A close-up photograph. Skin tone: FST IV: 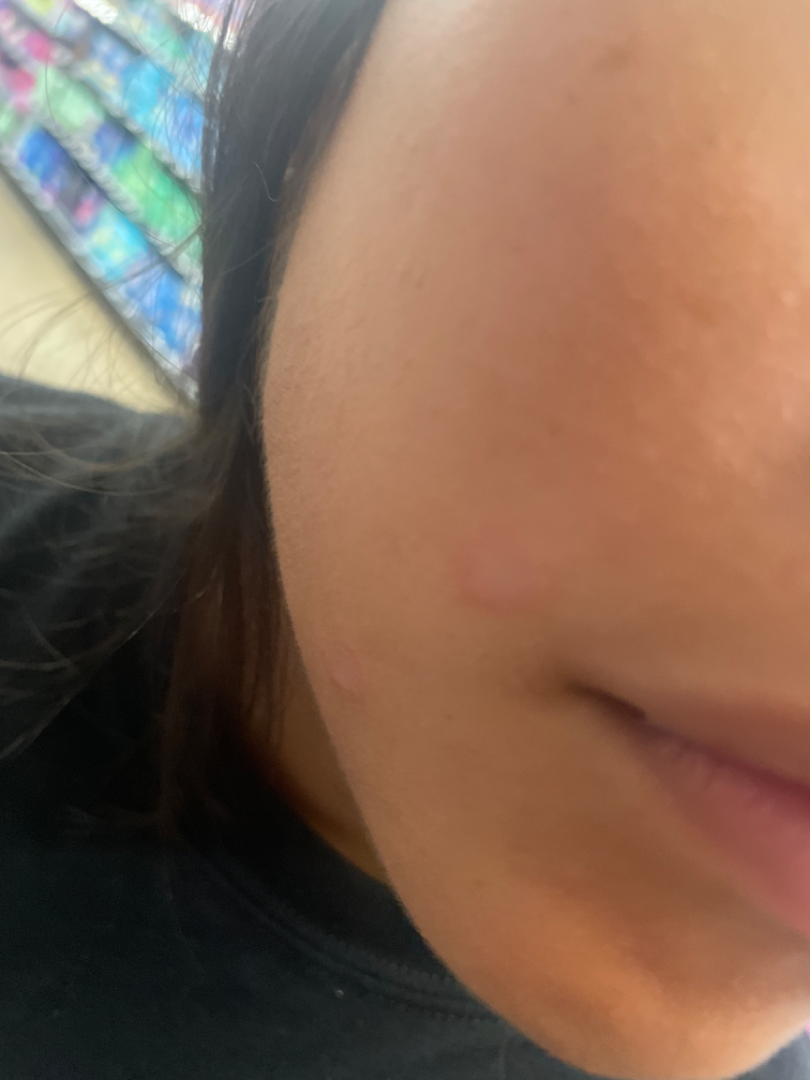The condition could not be reliably identified from the image.